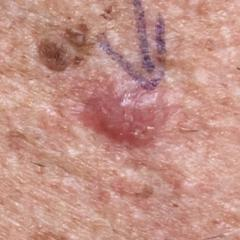The chart records prior skin cancer (patient or family), pesticide exposure, alcohol use, and prior malignancy (patient or family). A clinical photograph showing a skin lesion. A male patient in their early 50s. The patient is skin type II. Located on the chest. The lesion measures 9 × 5 mm. The patient reports that the lesion itches, is elevated, has grown, hurts, and has bled. On biopsy, the diagnosis was a skin cancer — a basal cell carcinoma.